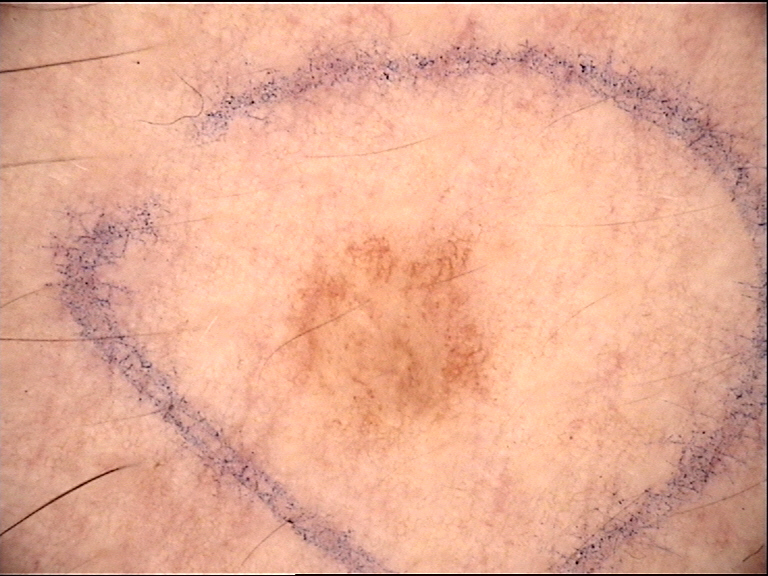label: dysplastic junctional nevus (expert consensus).